This image was taken at an angle: 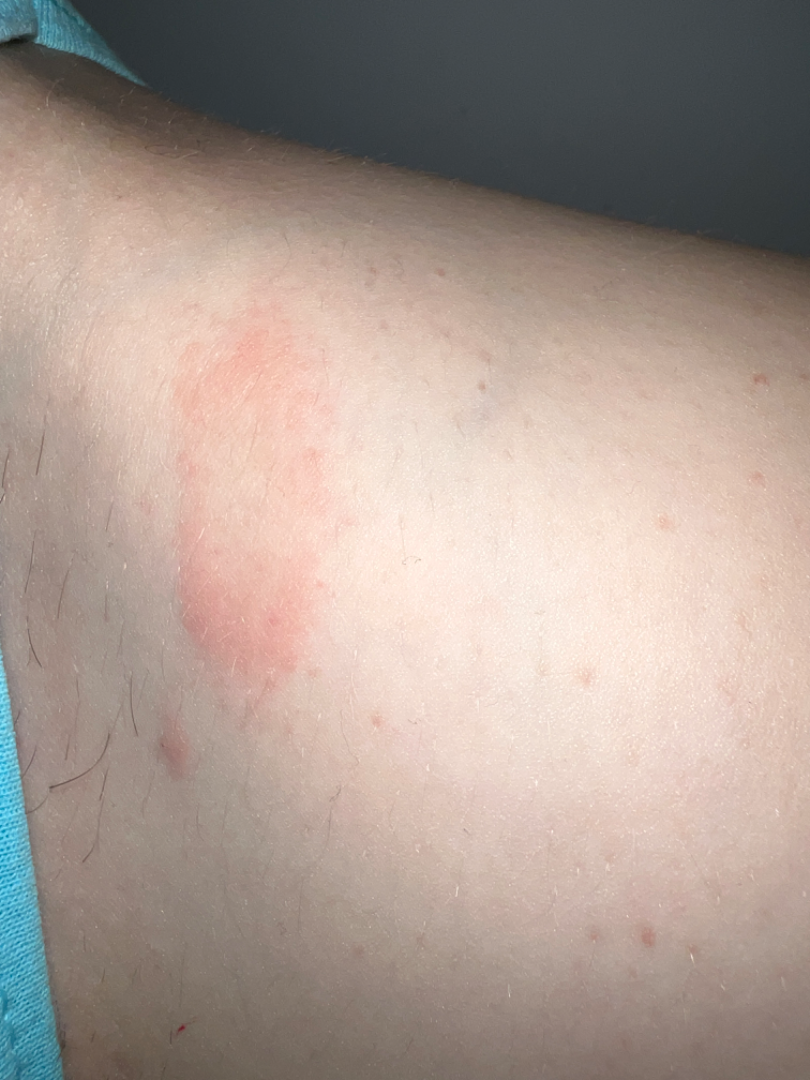  assessment: indeterminate from the photograph